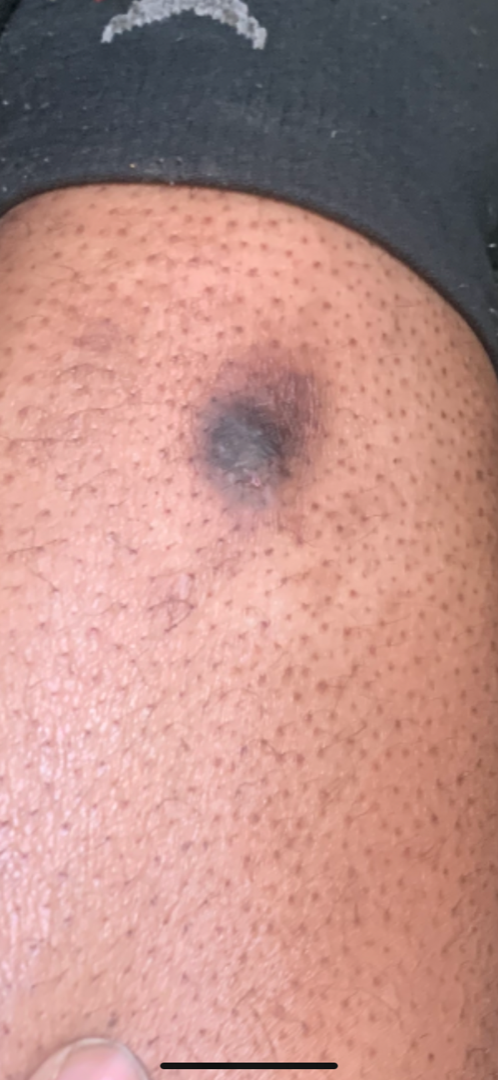The photograph is a close-up of the affected area.
On remote dermatologist review, the primary impression is Dermatofibroma; an alternative is Lichen Simplex Chronicus; a more distant consideration is Scar Condition.